The leg is involved · the photograph was taken at a distance · the patient is a female aged 50–59 — 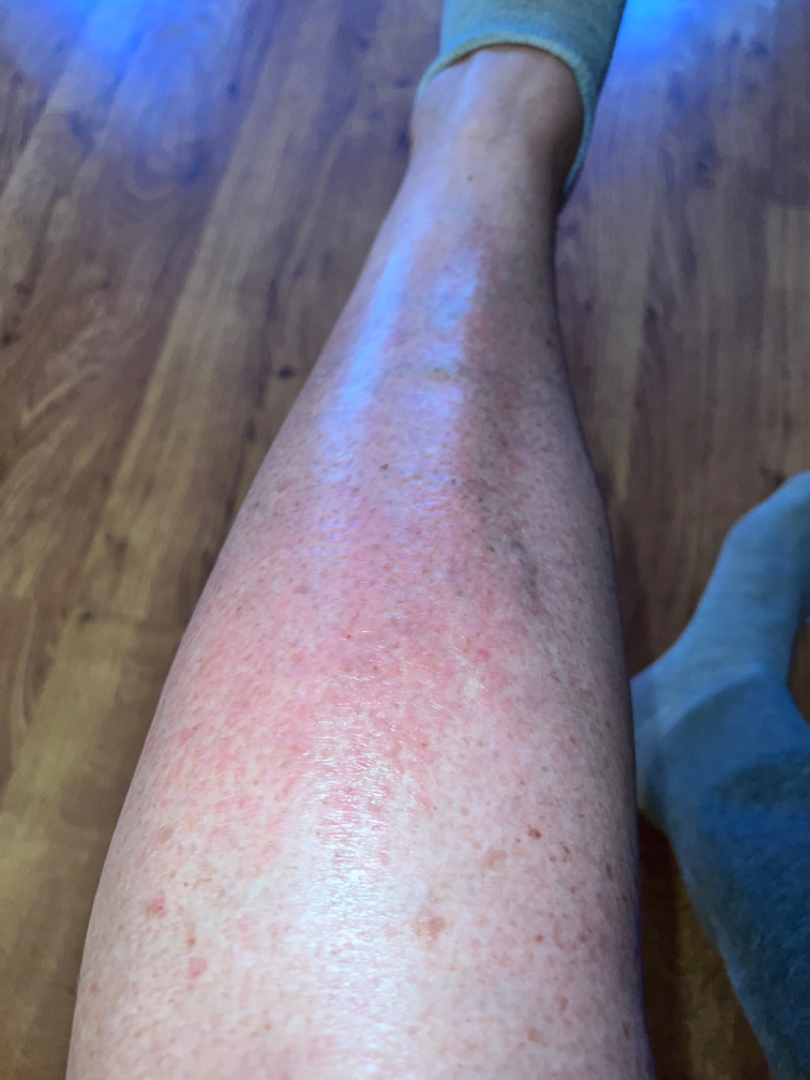Q: Reported symptoms?
A: bothersome appearance, darkening and itching
Q: Constitutional symptoms?
A: joint pain and fatigue
Q: Patient's own categorization?
A: a rash
Q: What is the lesion texture?
A: raised or bumpy
Q: What is the dermatologist's impression?
A: the leading consideration is Allergic Contact Dermatitis; an alternative is Amyloidosis of skin; also consider Pretibial myxedema